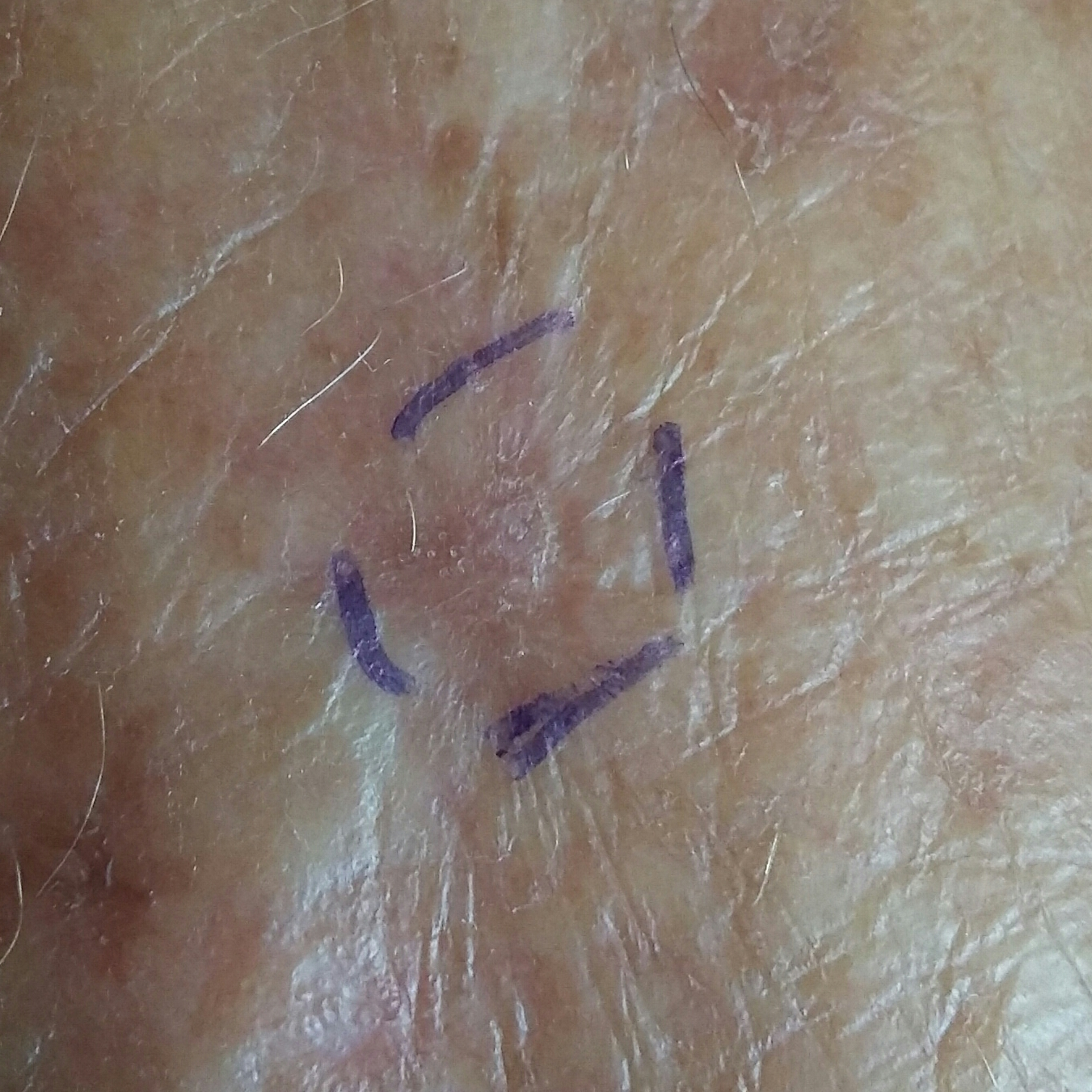Clinically diagnosed as an actinic keratosis.